Dermoscopy of a skin lesion: 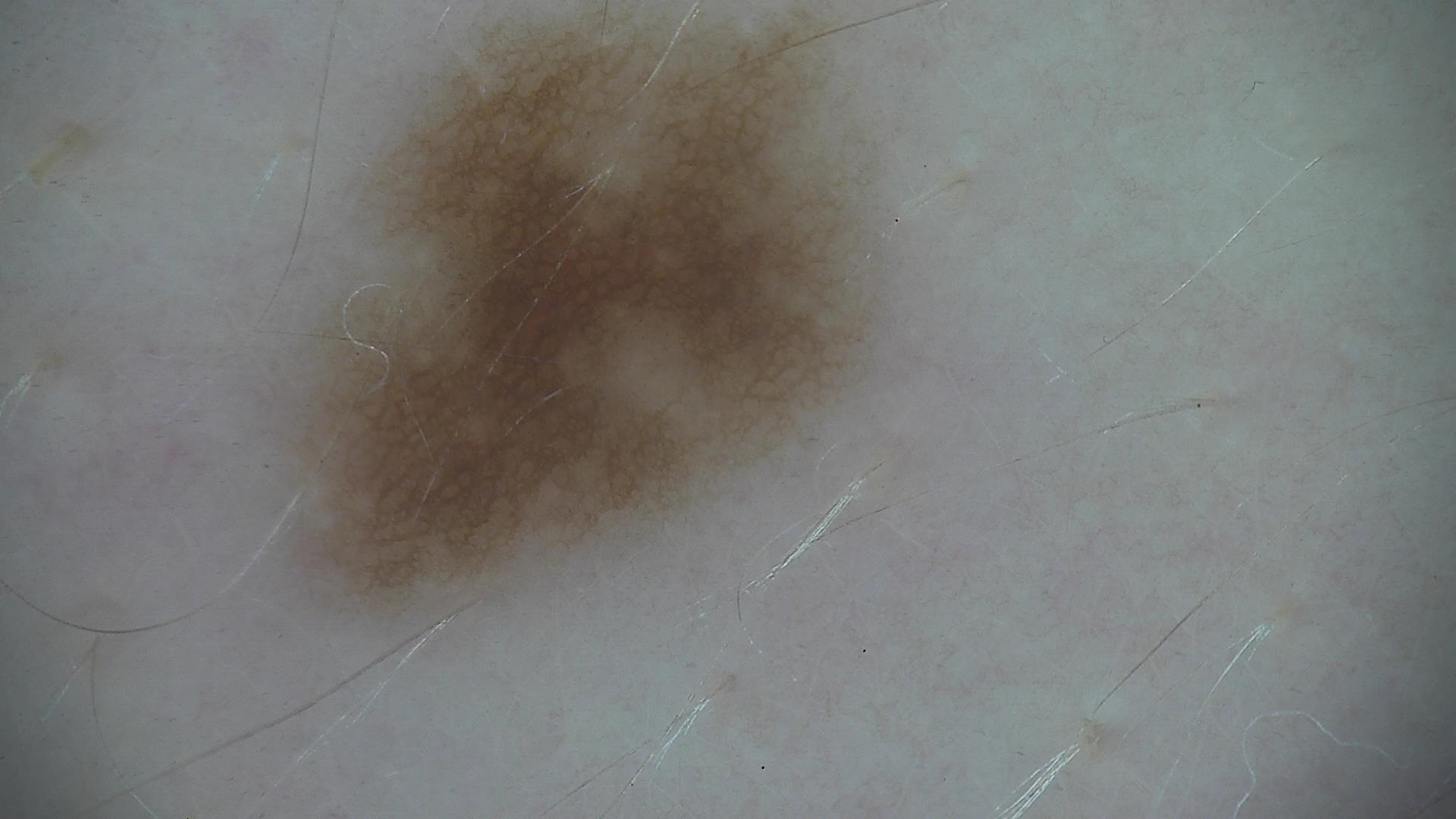Q: What is this lesion?
A: dysplastic junctional nevus (expert consensus)